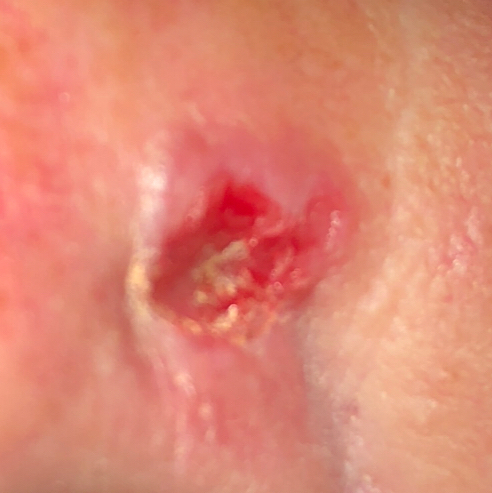| key | value |
|---|---|
| image type | clinical photograph |
| exposures | pesticide exposure, prior malignancy (patient or family), no tobacco use, no prior skin cancer (patient or family) |
| patient | female, 58 years of age |
| FST | II |
| location | the nose |
| lesion diameter | approx. 11 × 7 mm |
| symptoms | bleeding, growth, pain, elevation, itching / no change in appearance |
| pathology | basal cell carcinoma (biopsy-proven) |